Reported duration is less than one week, the contributor reports the lesion is flat, the patient described the issue as a rash, the affected area is the arm, the photograph was taken at a distance — 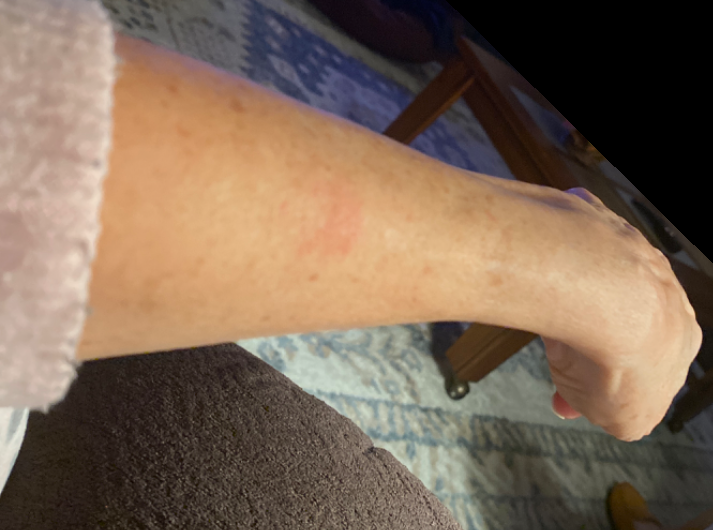assessment=indeterminate from the photograph.